This is a close-up image. The lesion is associated with enlargement, burning and itching. Texture is reported as raised or bumpy. The patient is a female aged 50–59. Located on the back of the torso, front of the torso, back of the hand and arm. The patient considered this a rash. The condition has been present for less than one week: 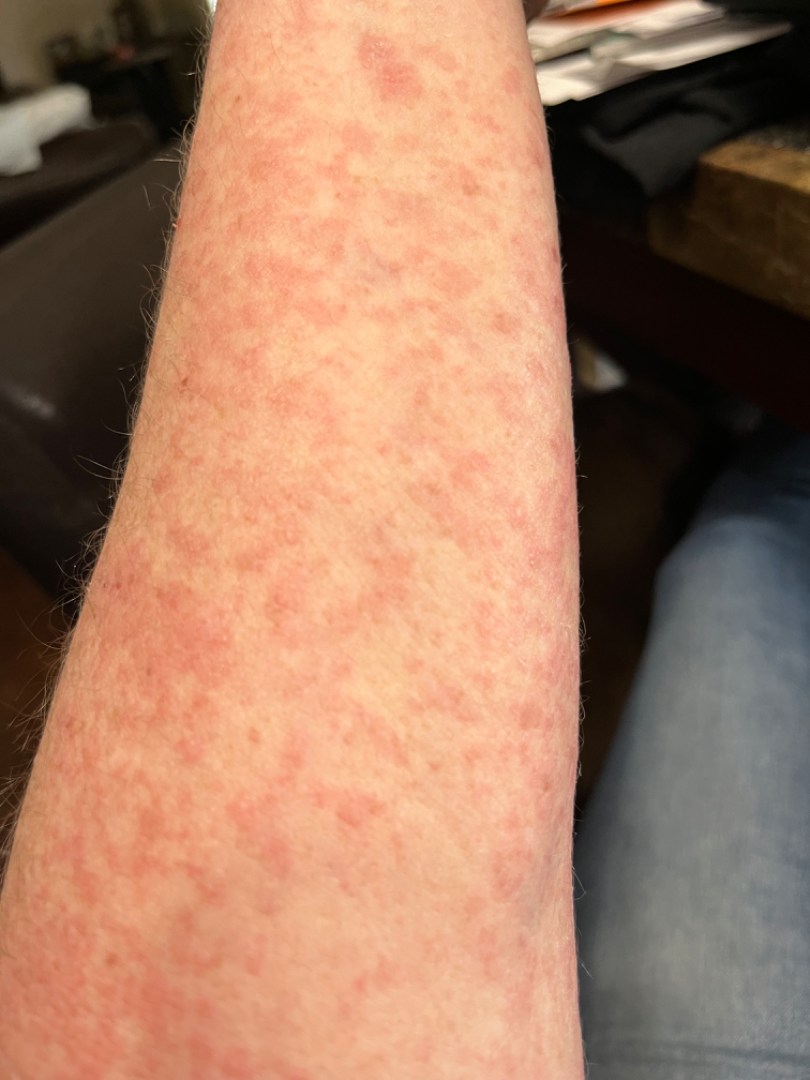Viral Exanthem and Drug Rash were considered with similar weight; less likely is Allergic Contact Dermatitis.